A male patient 60 years old; a skin lesion imaged with a dermatoscope — 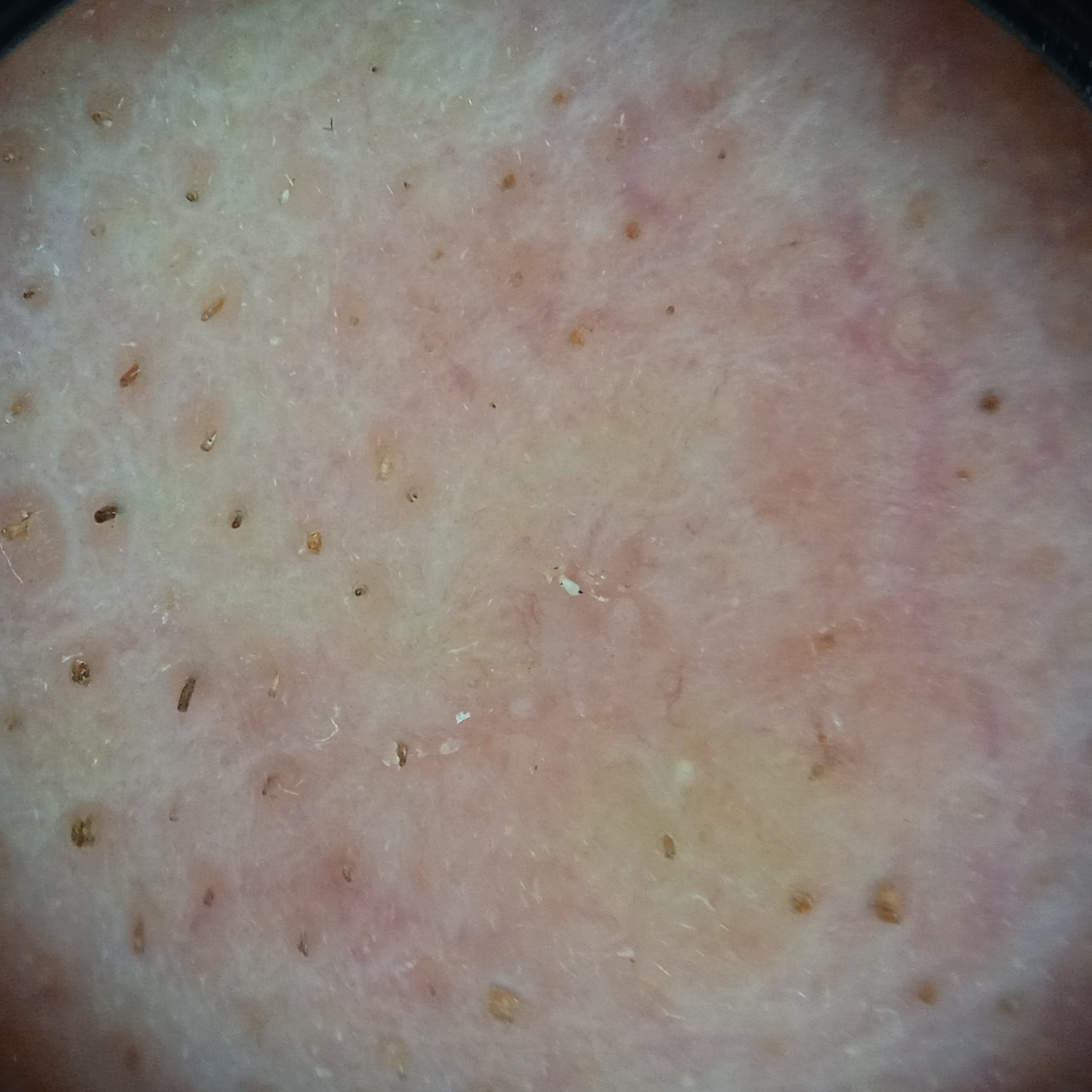Clinical context:
Located on the face. Measuring roughly 8.5 mm.
Conclusion:
On biopsy, the diagnosis was a basal cell carcinoma, following excision, with a measured thickness of 1.7 mm.